Close-up view. The lesion involves the top or side of the foot and sole of the foot. Female subject, age 40–49.
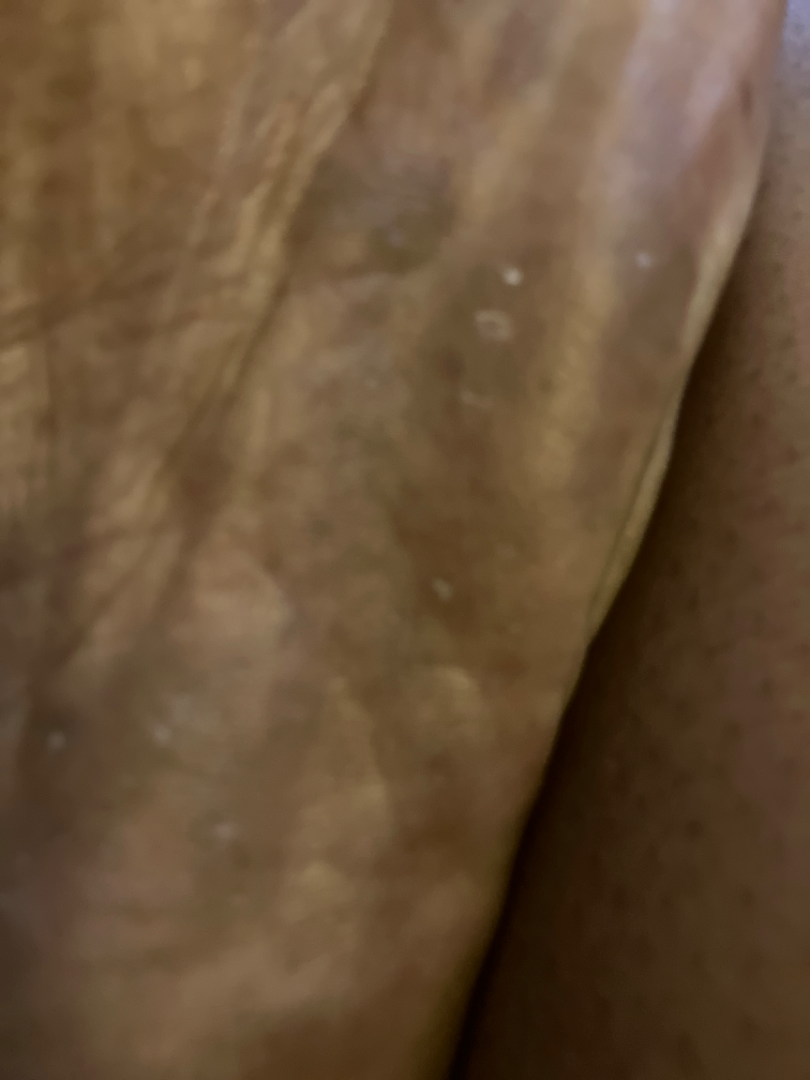Most likely Psoriasis; possibly Keratoderma; less probable is Tinea; a more distant consideration is Eczema.